Reported lesion symptoms include enlargement; the patient described the issue as a rash; the lesion involves the arm and leg; this image was taken at an angle; texture is reported as flat; no relevant systemic symptoms; the condition has been present for more than one year — 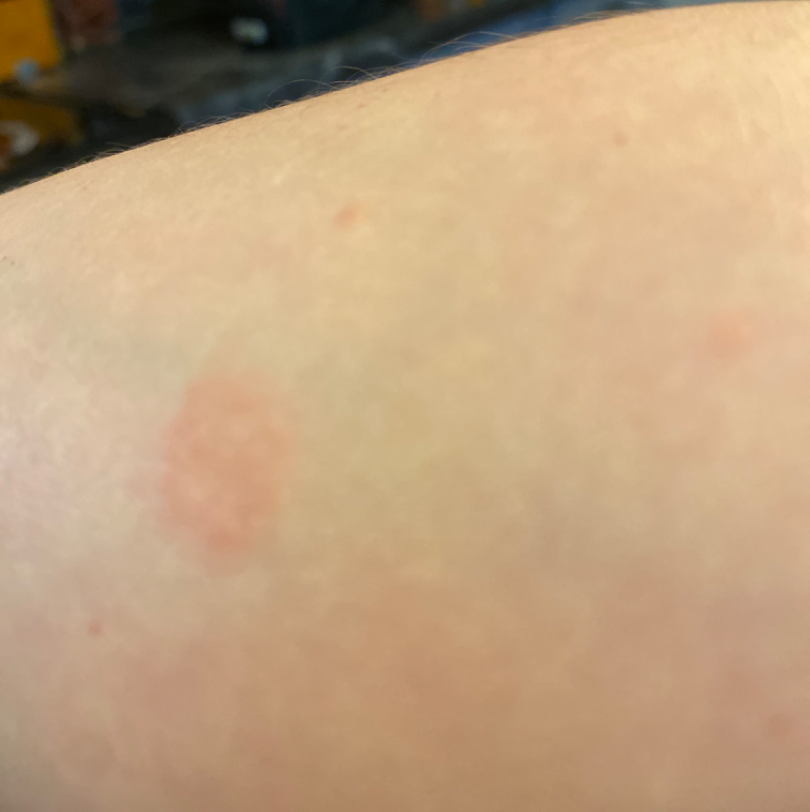Q: What was the assessment?
A: indeterminate